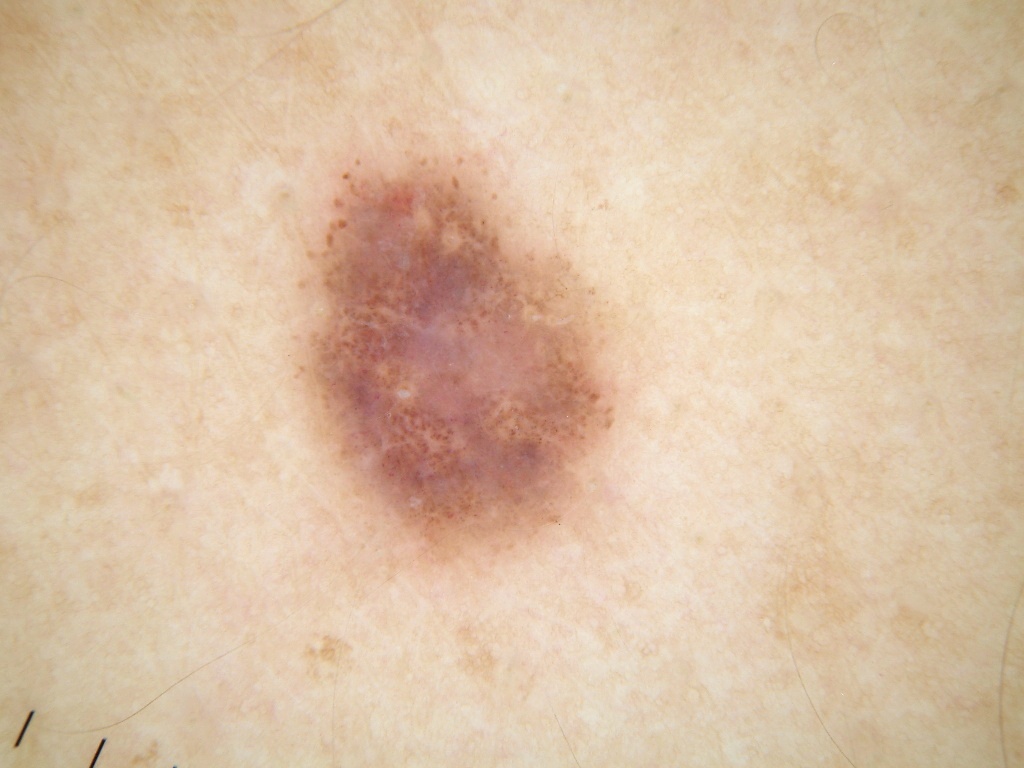Q: What is the imaging modality?
A: dermoscopy of a skin lesion
Q: Who is the patient?
A: male, in their mid-30s
Q: What does dermoscopy show?
A: milia-like cysts and globules
Q: What is the lesion's bounding box?
A: 291 132 617 570
Q: What is this lesion?
A: a melanocytic nevus, a benign skin lesion